The lesion involves the arm. The contributor reports the lesion is raised or bumpy and fluid-filled. Reported lesion symptoms include itching. Present for less than one week. Close-up view. The patient described the issue as a rash: 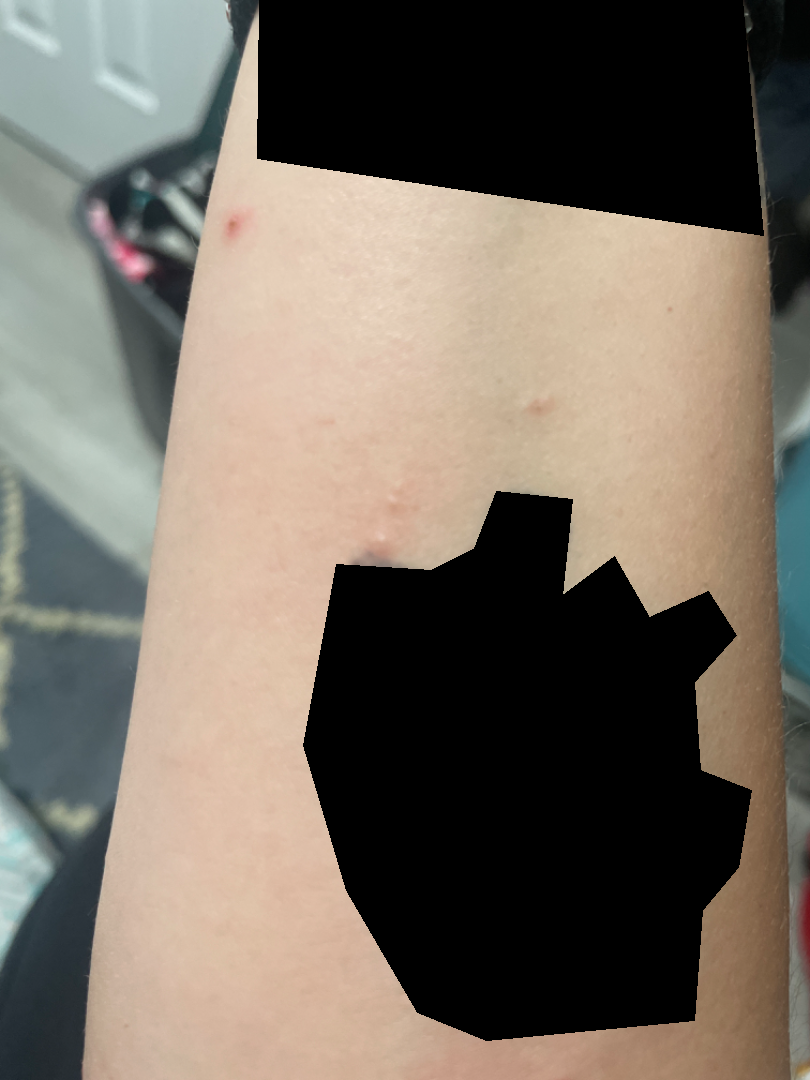The dermatologist could not determine a likely condition from the photograph alone.